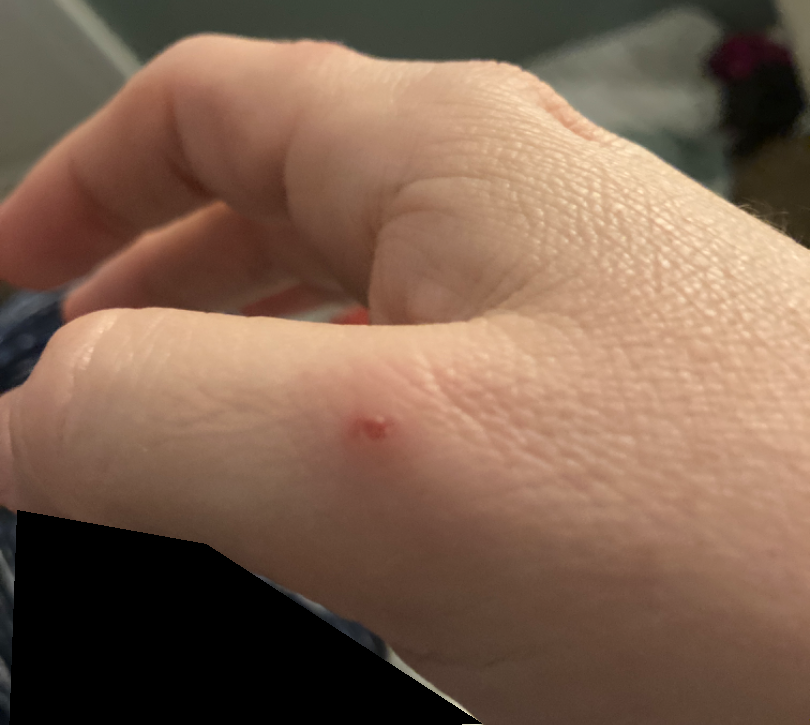Findings:
On teledermatology review, most likely Pyogenic granuloma; also on the differential is Abrasion, scrape, or scab; also raised was Insect Bite; a more distant consideration is Hemangioma; less probable is digital myxoid cyst.